The lesion is associated with burning, bothersome appearance and itching. The patient reported no systemic symptoms. A close-up photograph. The patient notes the lesion is rough or flaky and flat. Male patient, age 50–59. The affected area is the arm, back of the hand, palm and leg. Non-clinician graders estimated 3 on the Monk Skin Tone. The patient described the issue as a rash:
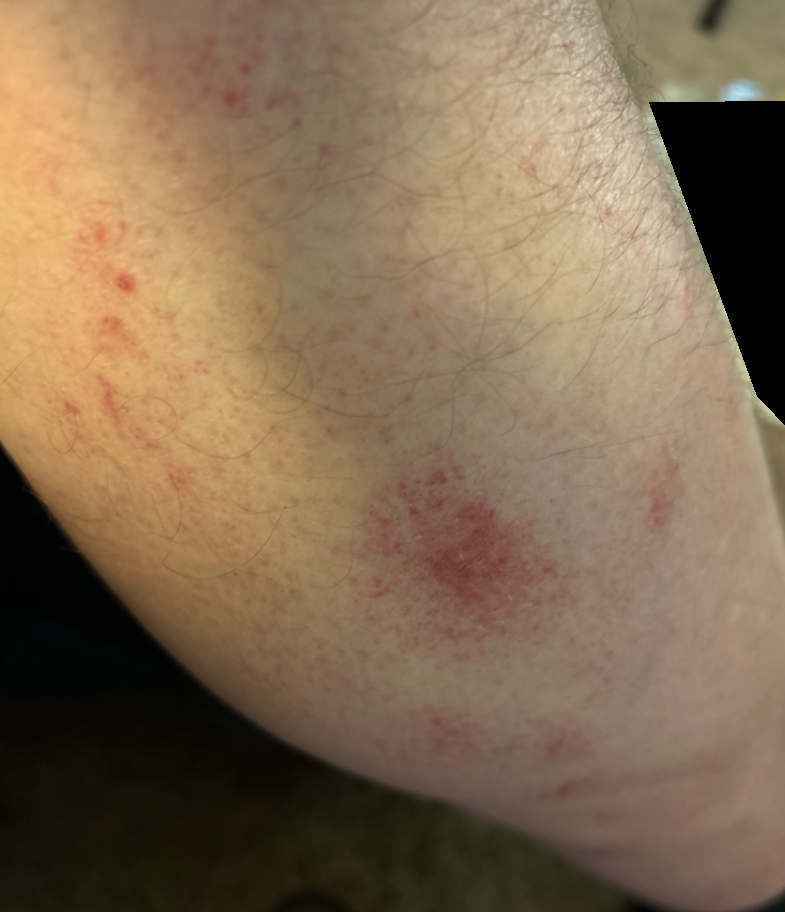diagnostic considerations — Pigmented purpuric eruption (favored).